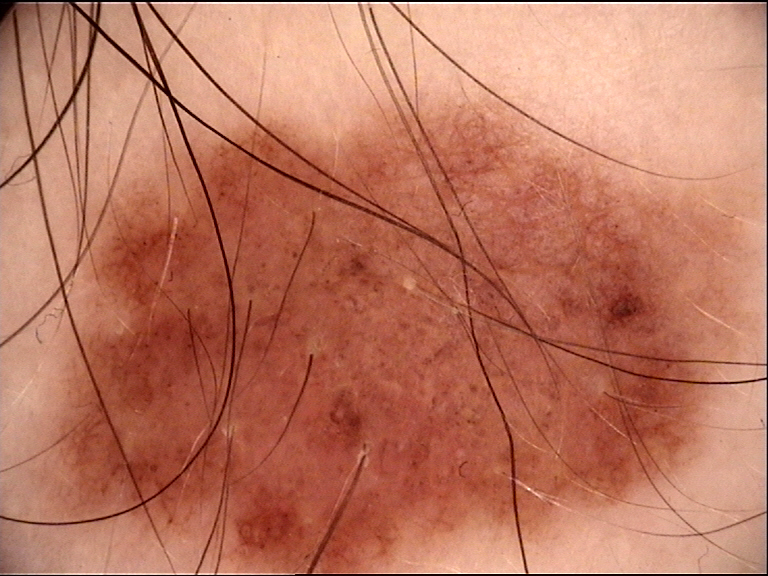diagnosis: dysplastic compound nevus (expert consensus).